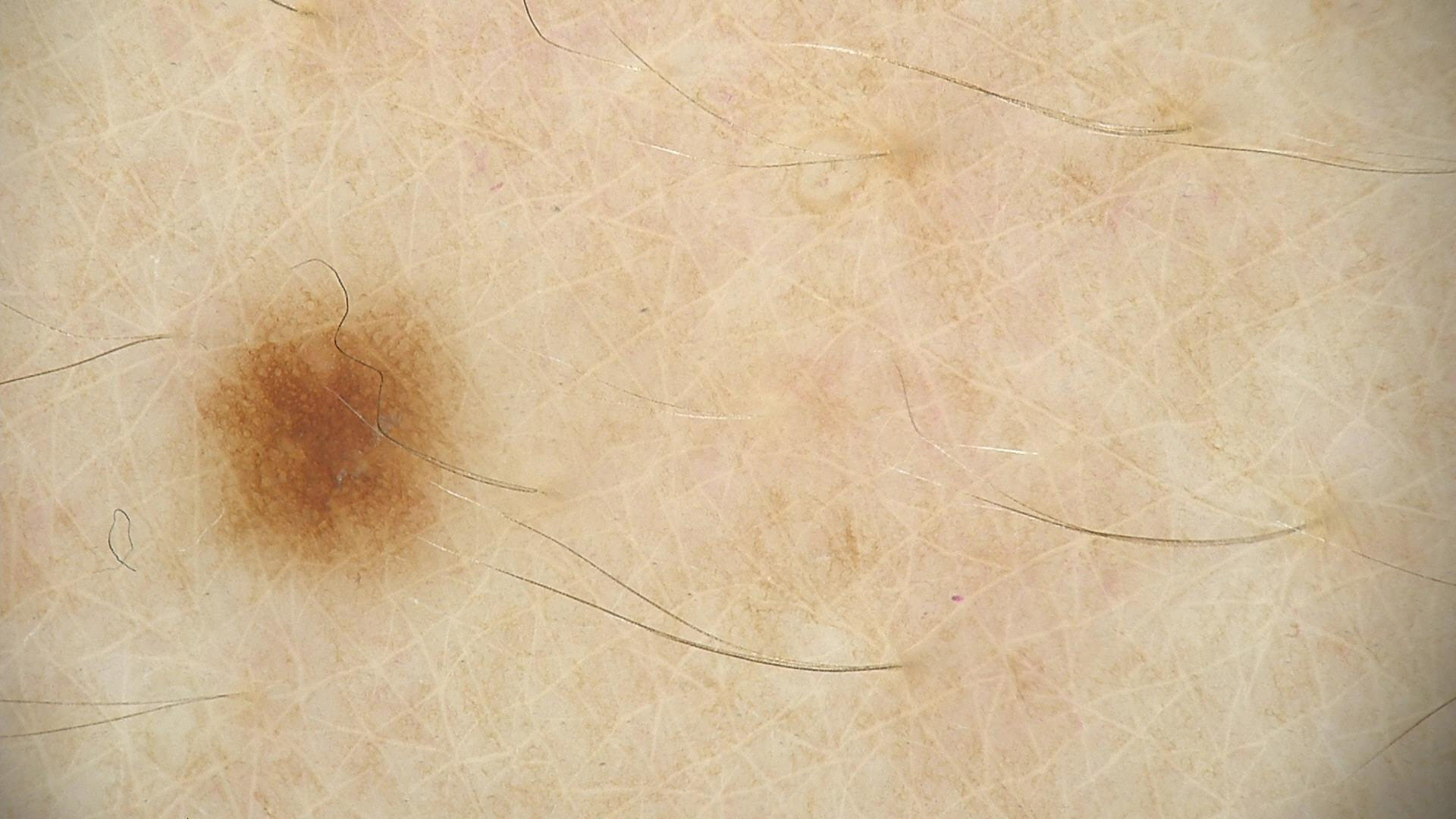A dermoscopic close-up of a skin lesion. The morphology is that of a banal lesion. Classified as a junctional nevus.